The patient describes having a moderate number of moles · imaged for a research study, with no referral diagnosis recorded · a male patient aged 77 · the patient reports a personal history of skin cancer and a personal history of cancer: 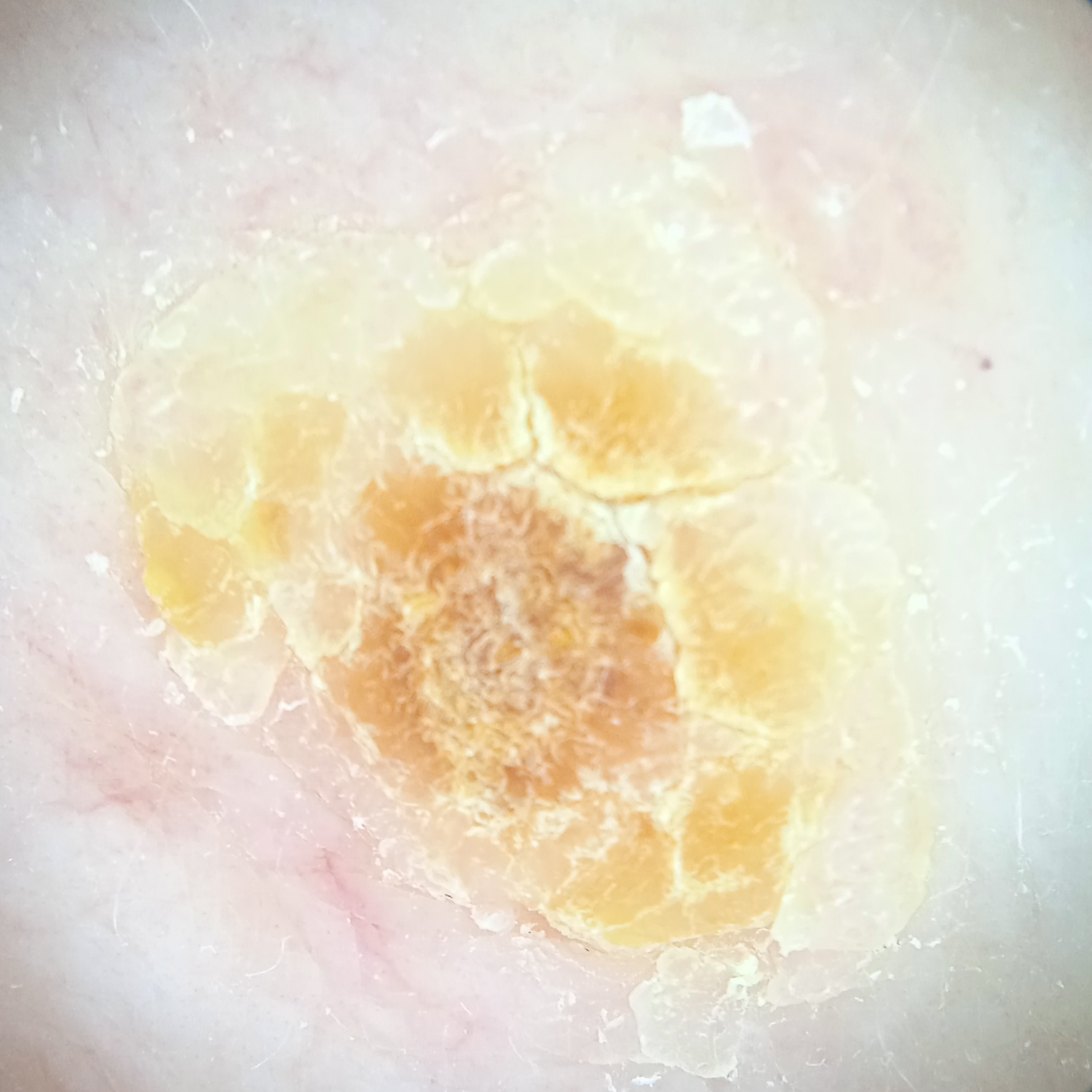Q: Where is the lesion?
A: the back
Q: What was the diagnosis?
A: actinic keratosis (dermatologist consensus)